A dermoscopic image of a skin lesion:
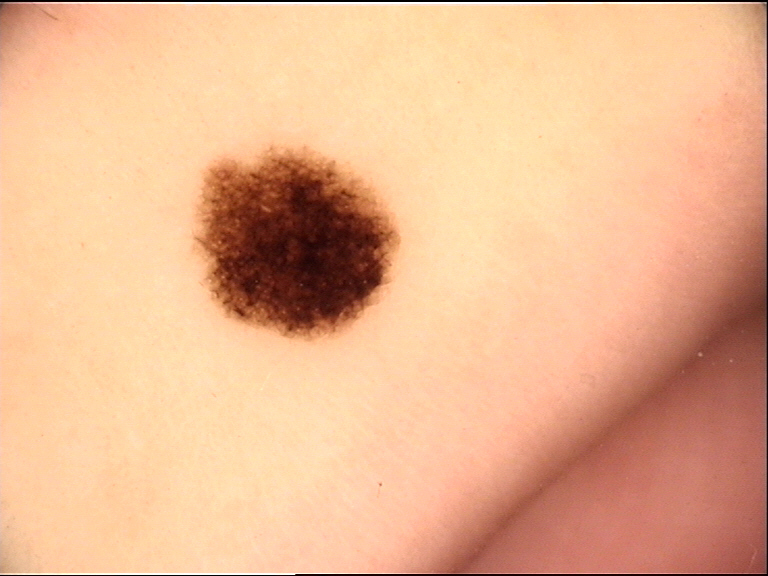The diagnostic label was a dysplastic compound nevus.